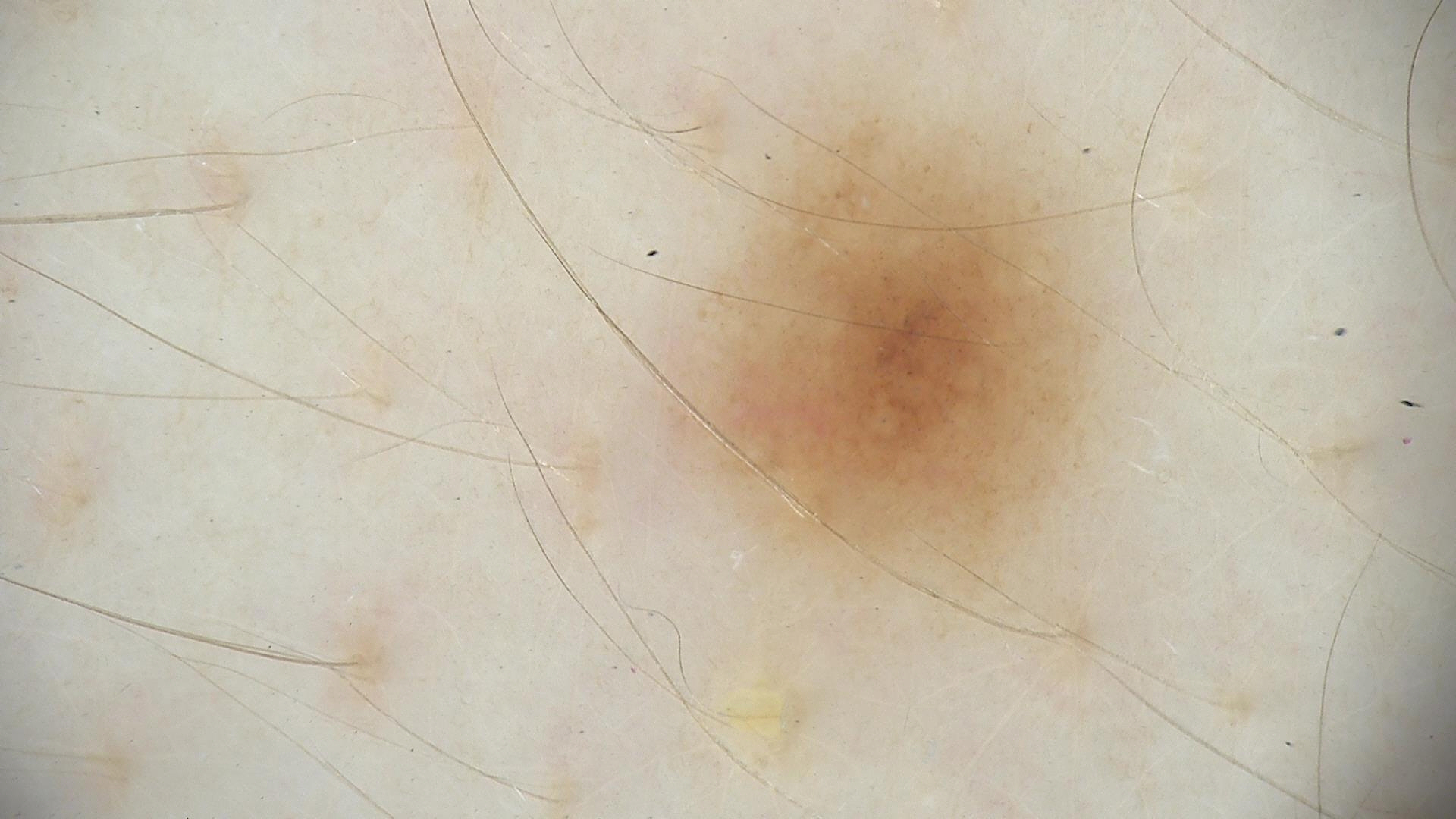modality = dermatoscopy, diagnosis = compound nevus (expert consensus).